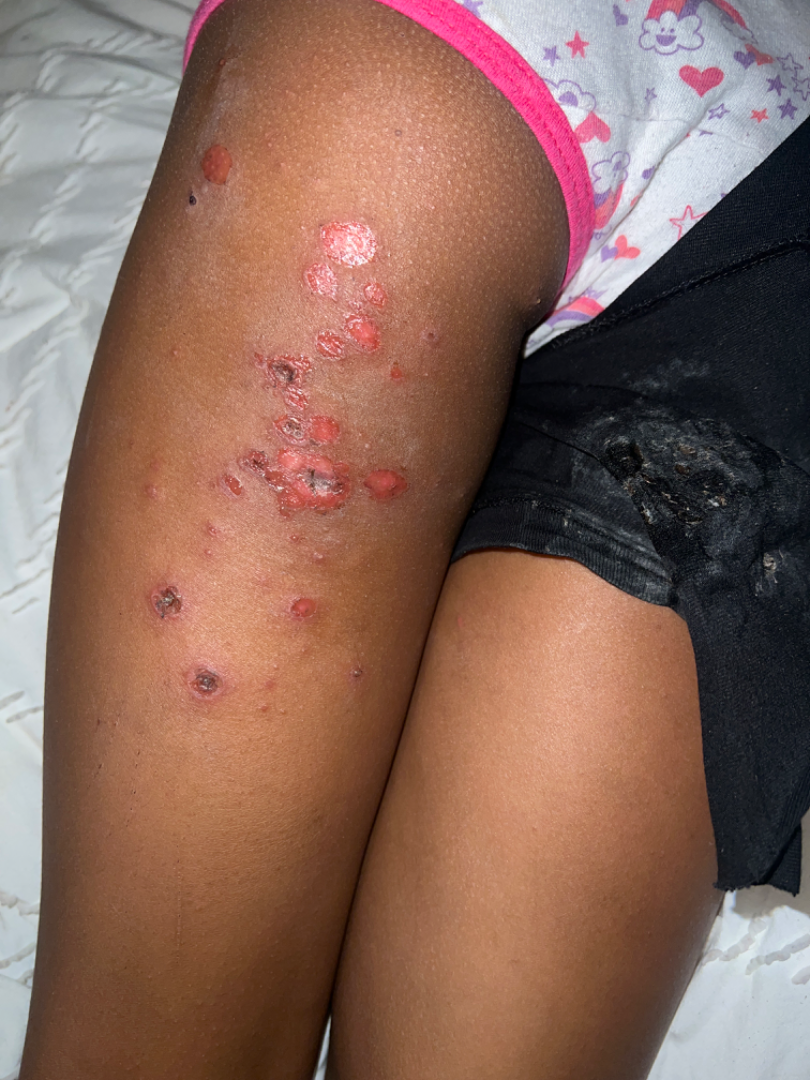Findings:
• affected area · leg and back of the torso
• photo taken · close-up
• texture · raised or bumpy and fluid-filled
• duration · less than one week
• skin tone · Fitzpatrick V; lay graders estimated Monk skin tone scale 5 or 7 (two reviewer pools disagreed)
• clinical impression · most consistent with Impetigo